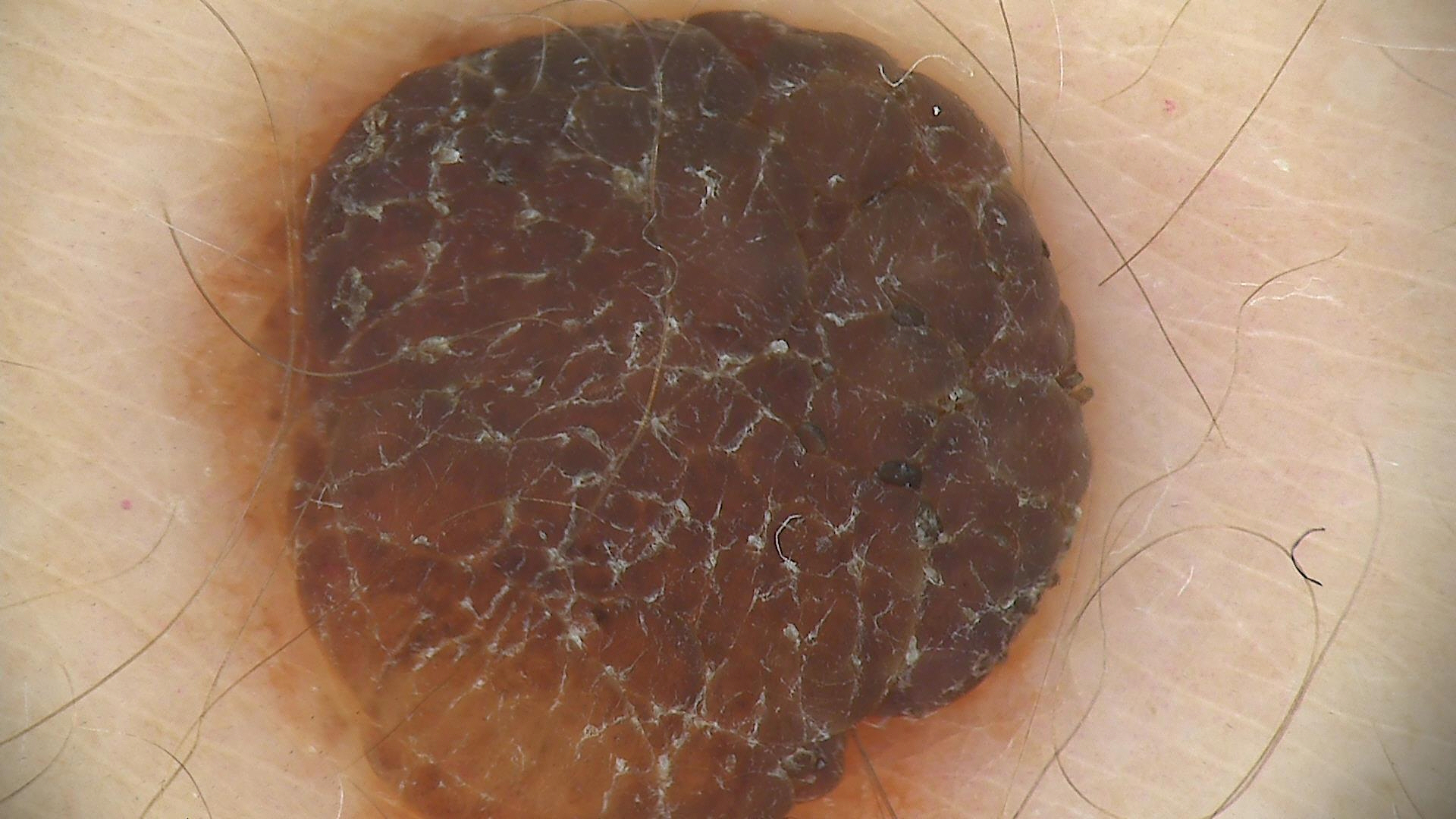Case: A dermatoscopic image of a skin lesion. This is a banal lesion. Conclusion: The diagnostic label was a compound nevus.